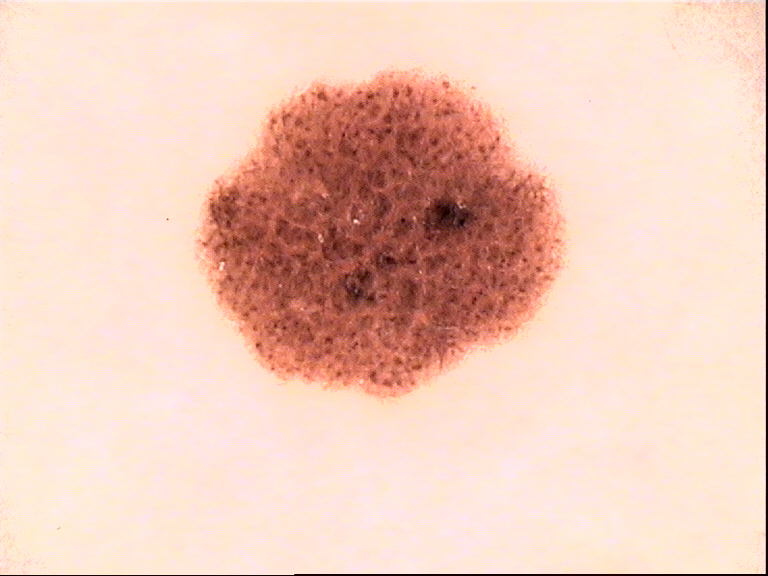A dermoscopic photograph of a skin lesion.
The diagnosis was a benign lesion — a dysplastic junctional nevus.